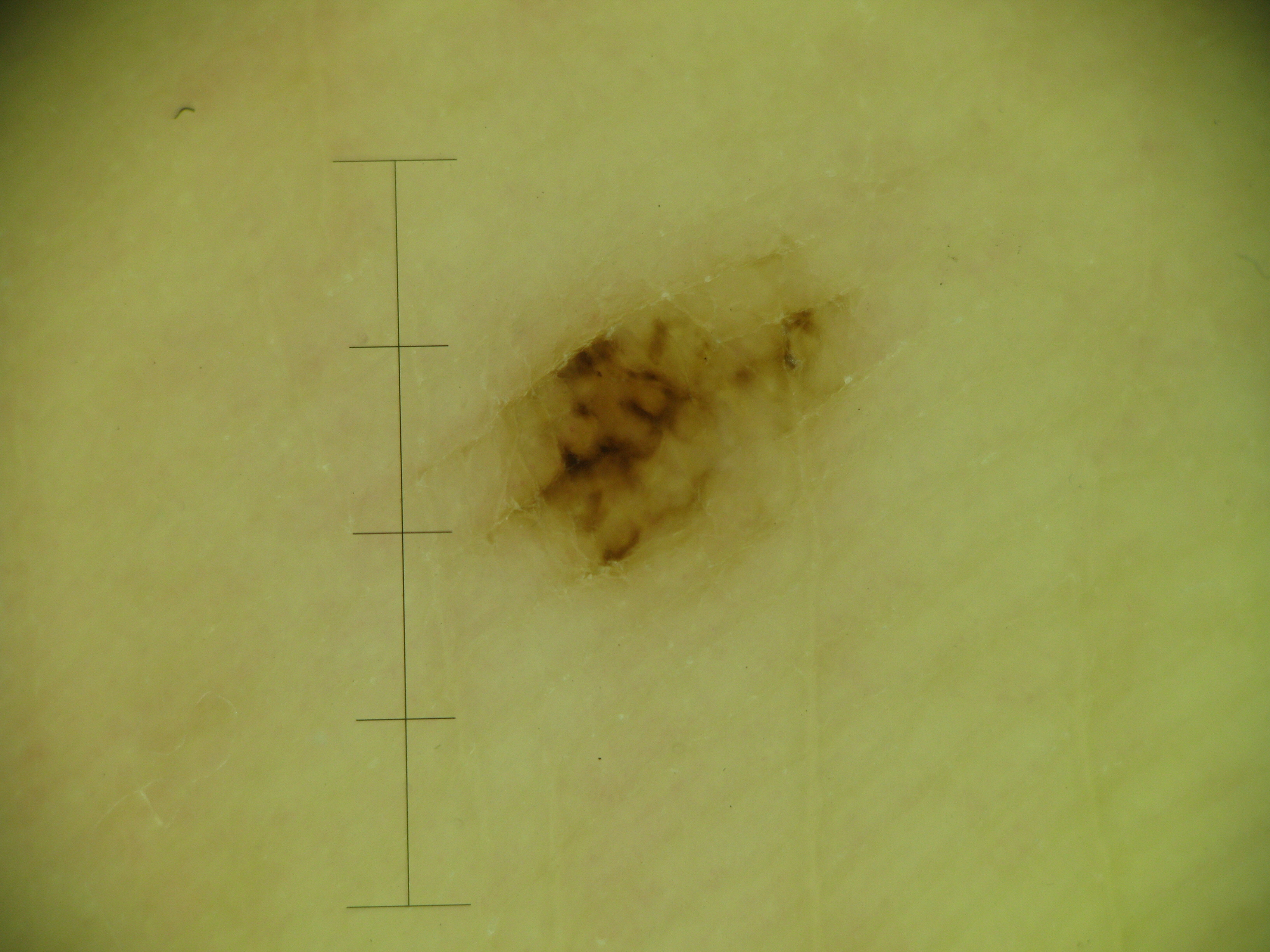A dermoscopic image of a skin lesion. This is a banal lesion. Consistent with an acral junctional nevus.